A dermoscopic view of a skin lesion:
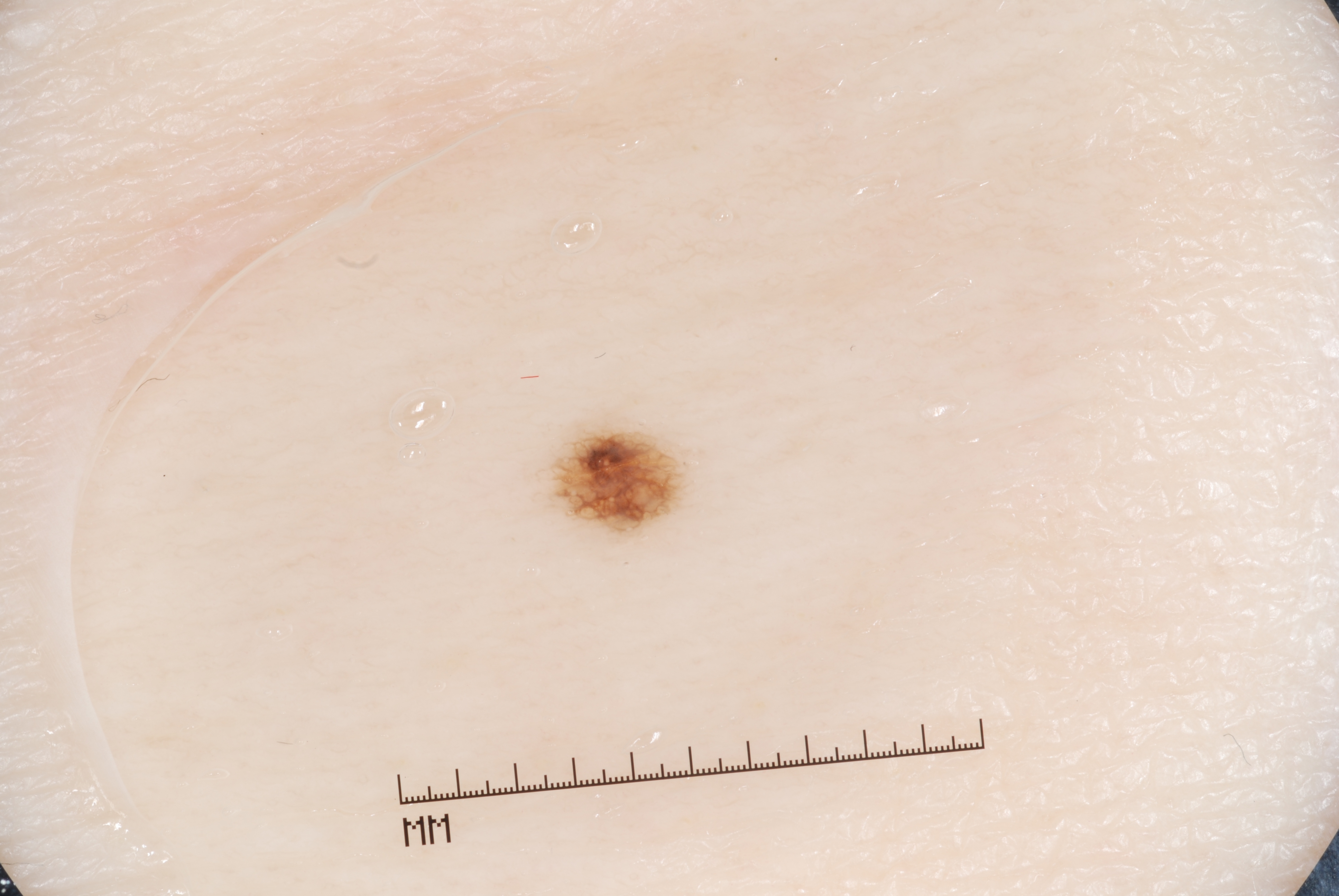Dermoscopically, the lesion shows pigment network, with no streaks, milia-like cysts, or negative network. The lesion is small relative to the field of view. In (x1, y1, x2, y2) order, the lesion occupies the region <bbox>534, 413, 690, 539</bbox>. Clinically diagnosed as a melanocytic nevus.